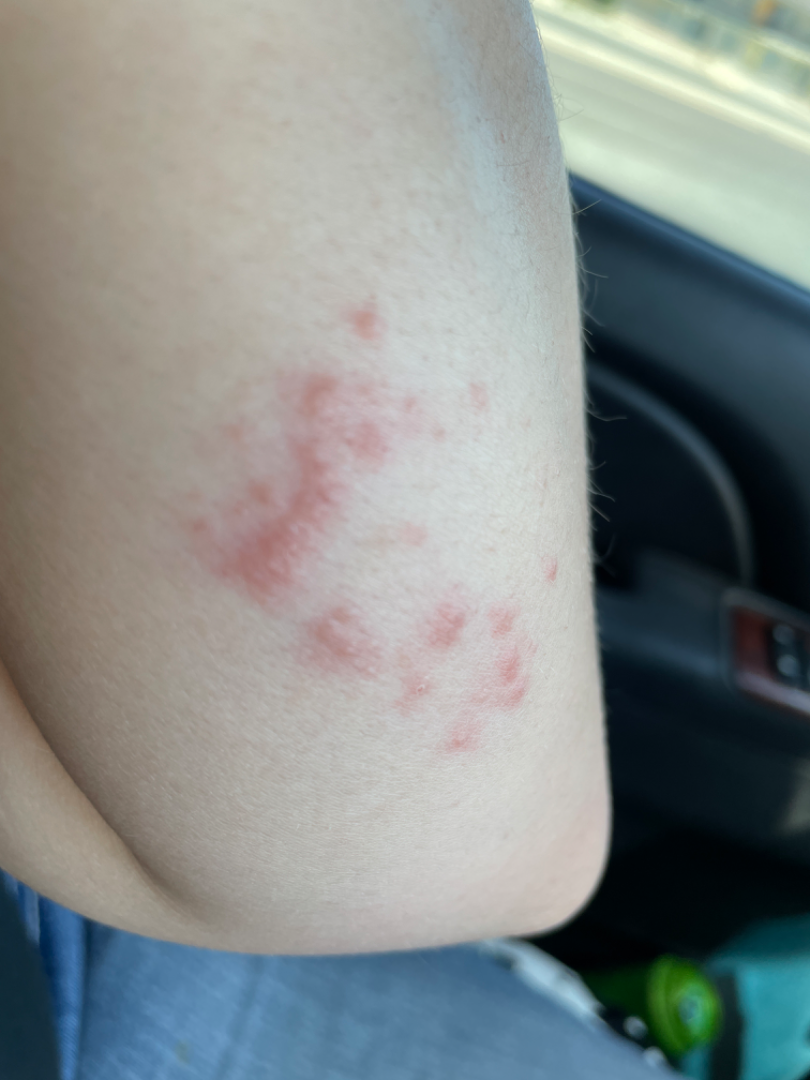Case summary:
• assessment · indeterminate